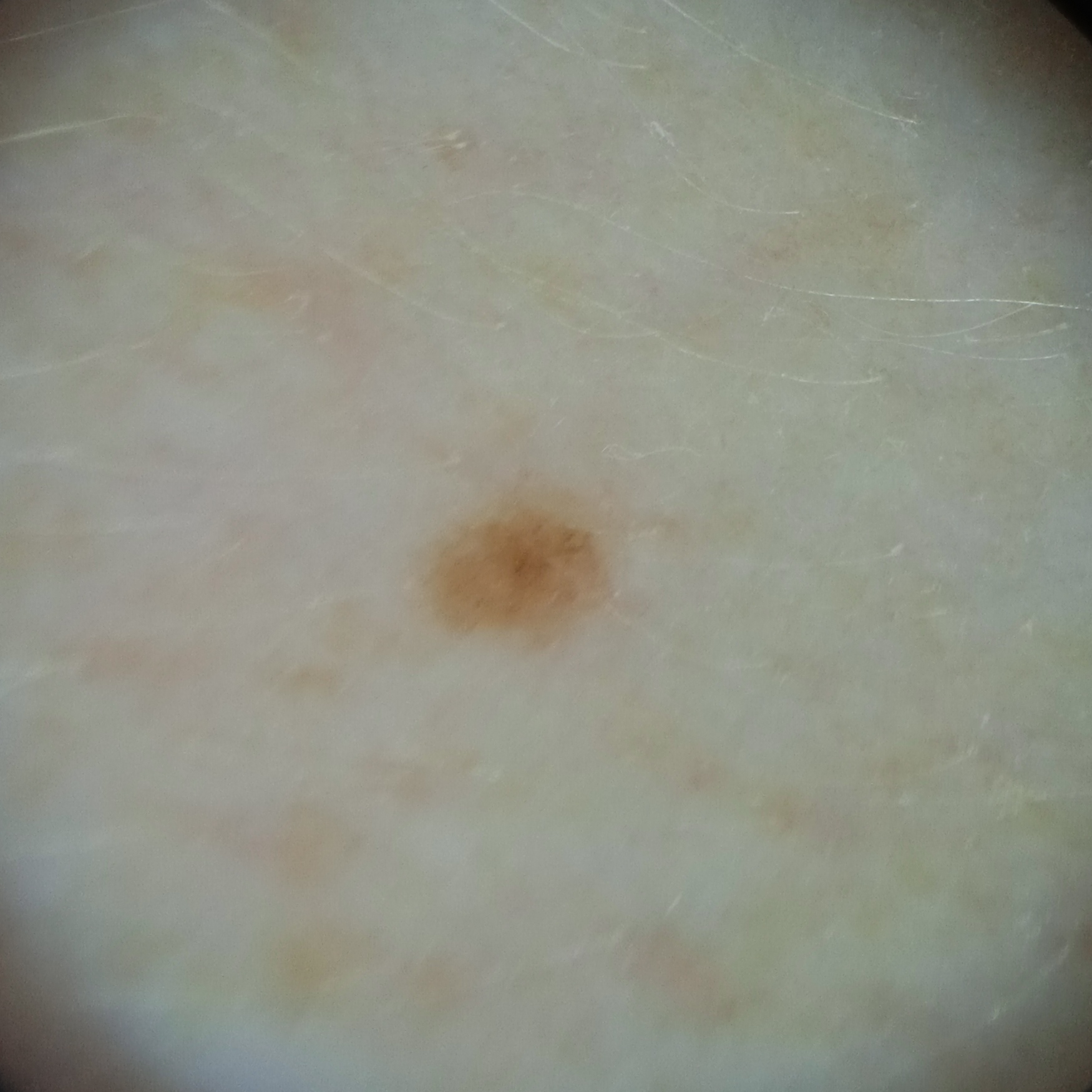The lesion was assessed as a melanocytic nevus.